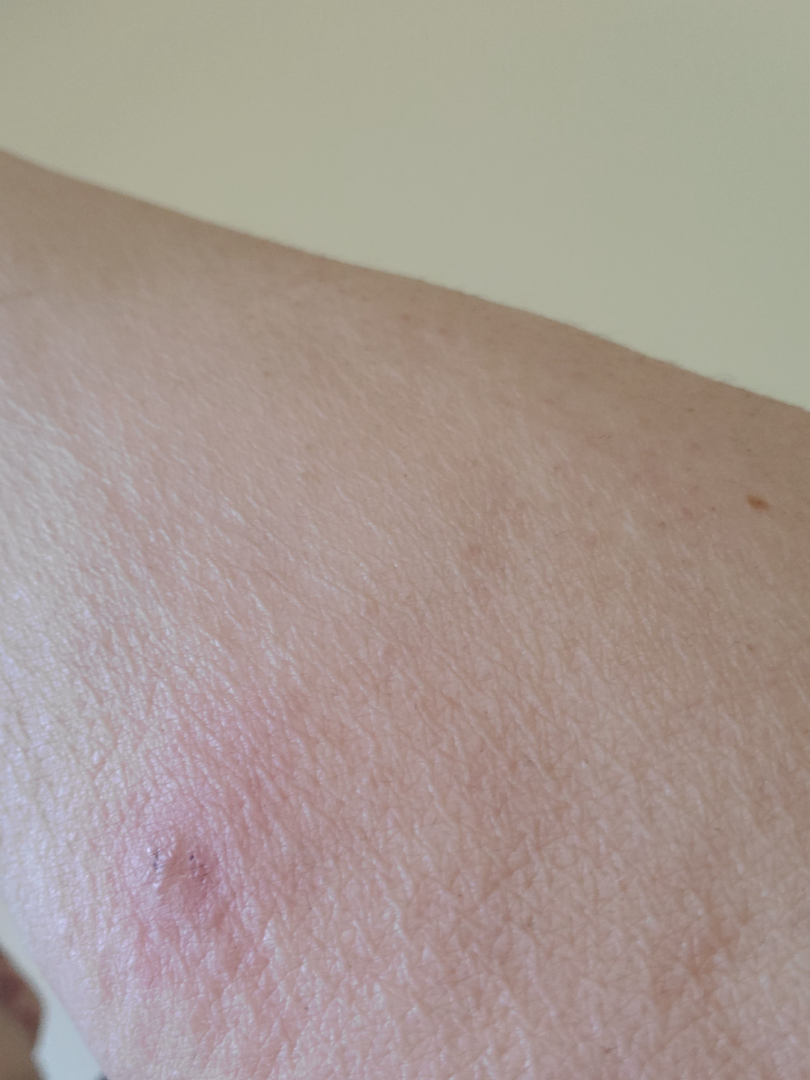assessment: indeterminate
body_site: arm
shot_type: at an angle
duration: about one day
patient: female, age 70–79
texture: raised or bumpy
symptoms: itching
patient_category: a rash